The patient is a female aged 40–49; located on the arm; the photograph was taken at a distance.
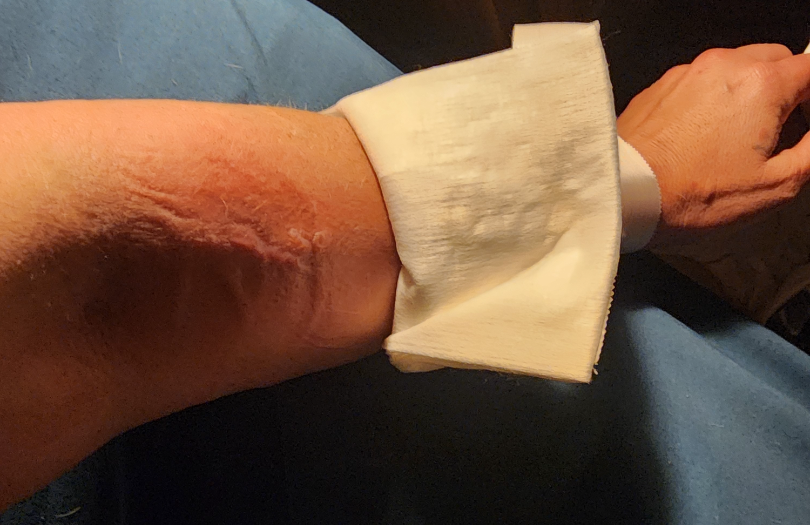The dermatologist could not determine a likely condition from the photograph alone. The patient described the issue as a rash. Present for about one day. Texture is reported as fluid-filled. The patient notes itching, pain and burning.